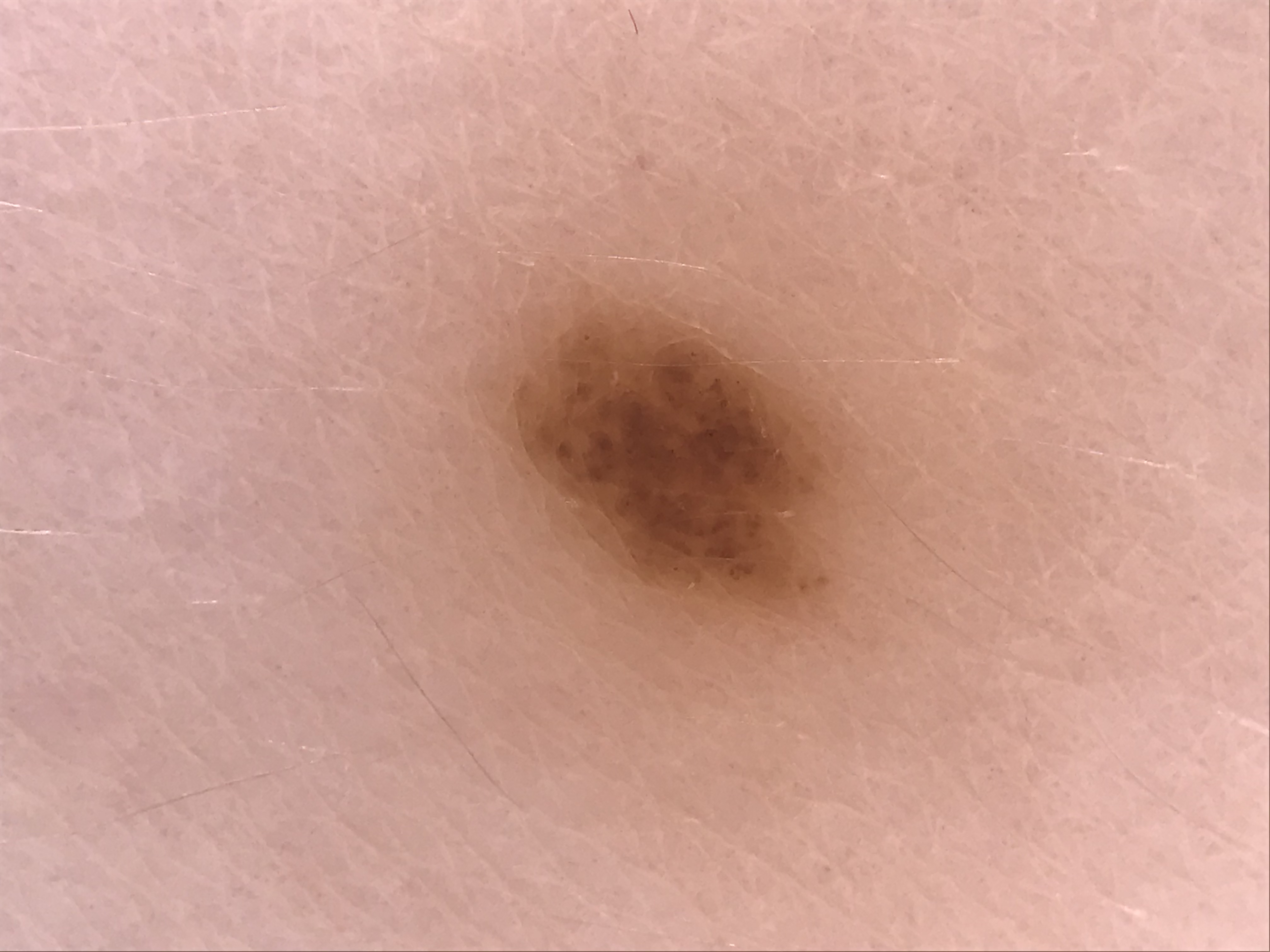The morphology is that of a banal lesion.
Labeled as a compound nevus.